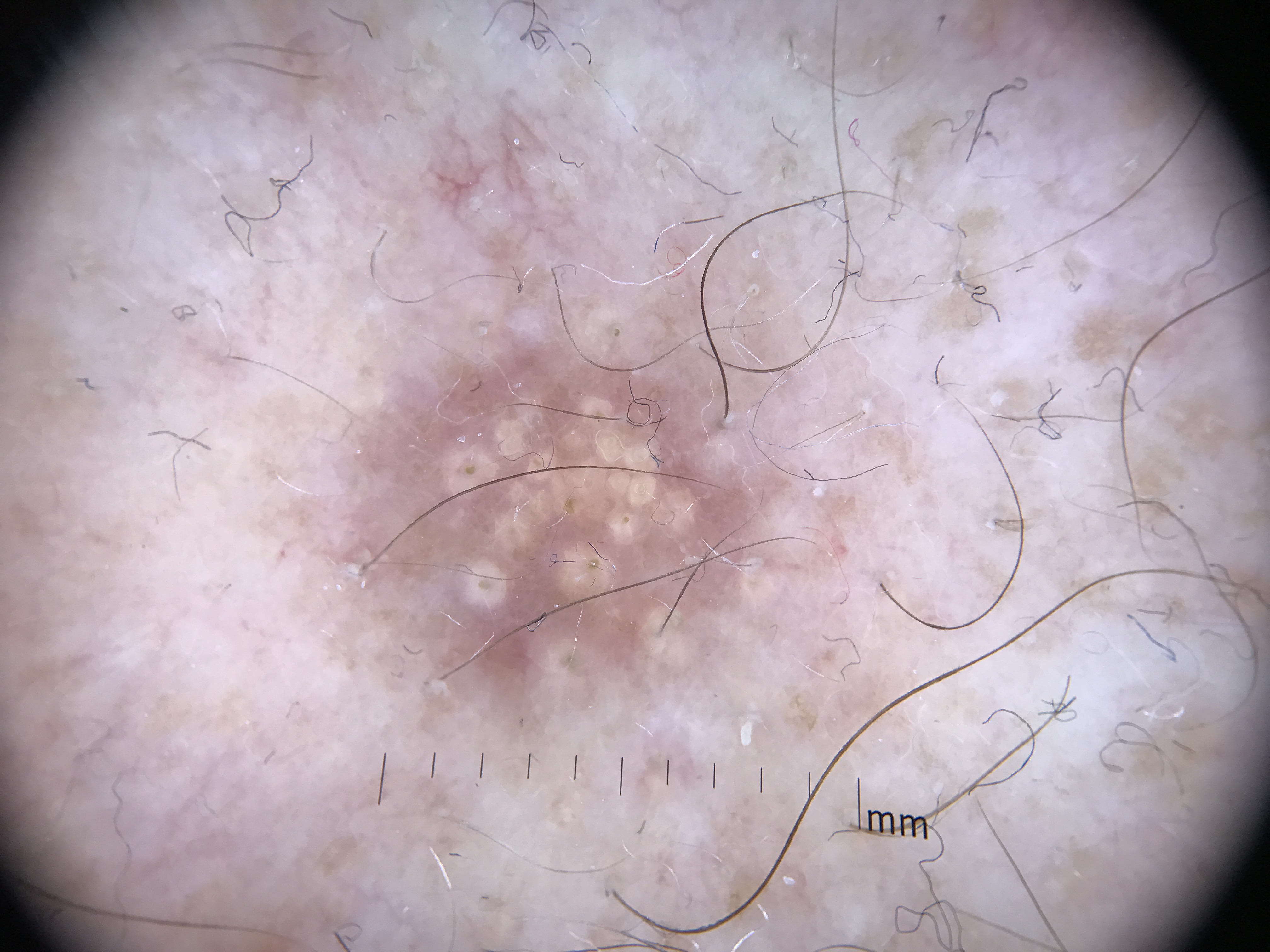modality: dermatoscopy; assessment: dermatofibroma (expert consensus).